A female subject in their 70s:
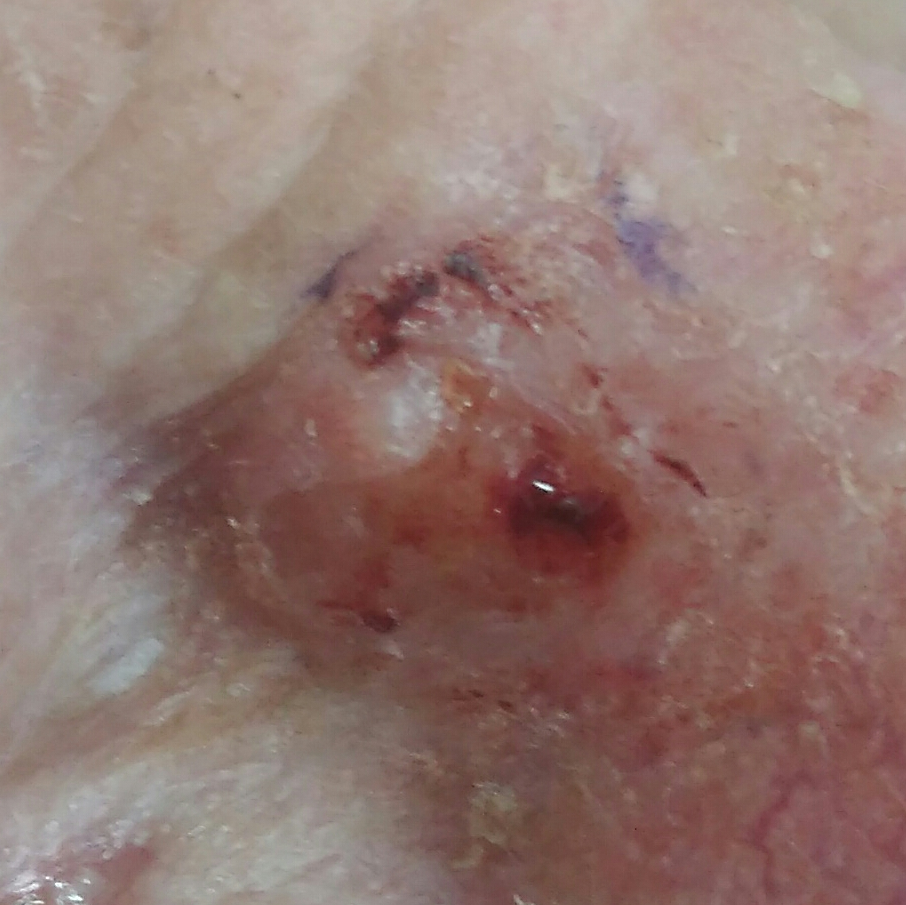Pathology:
The biopsy diagnosis was a basal cell carcinoma.